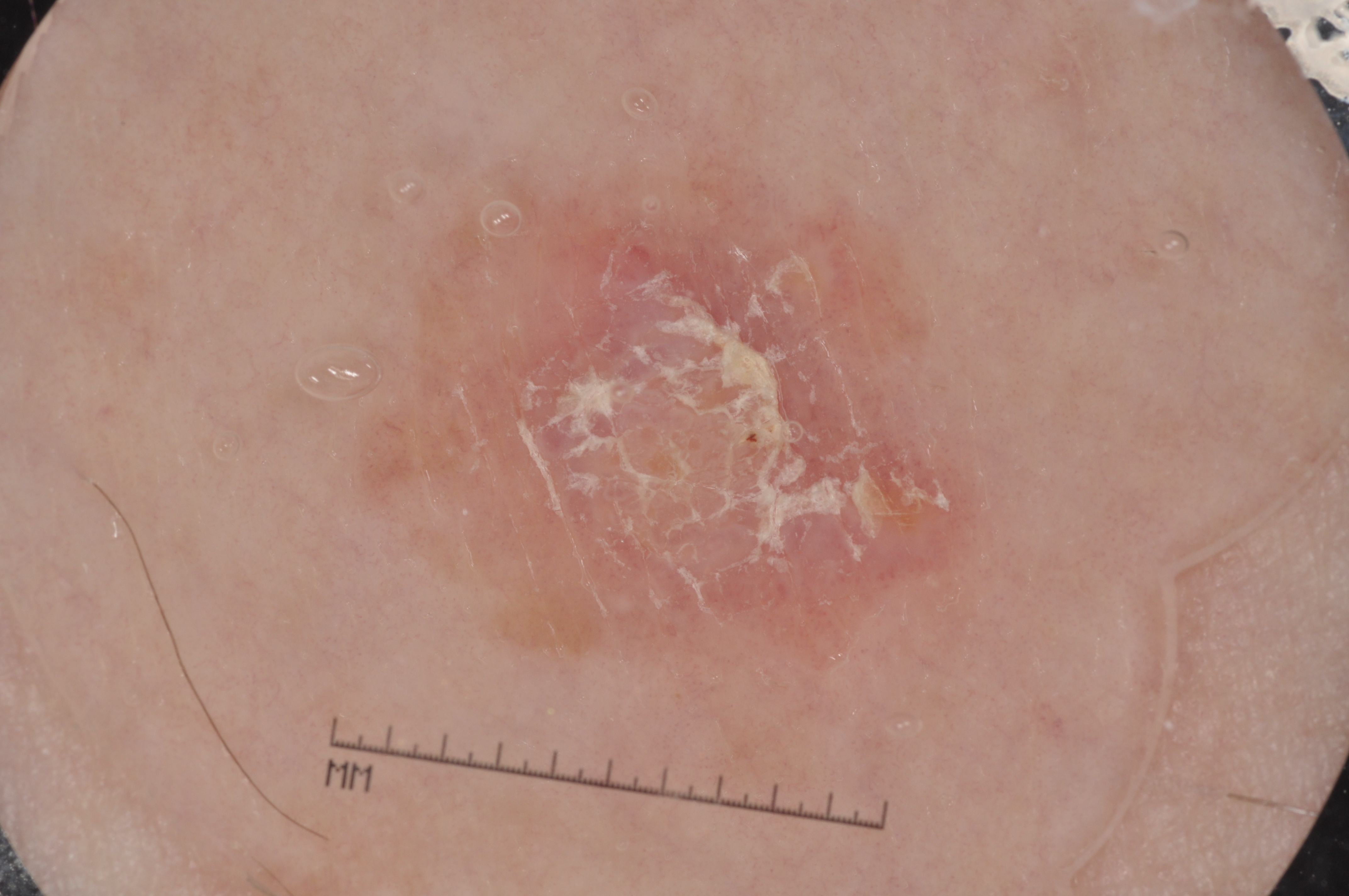Summary: A dermoscopic image of a skin lesion. In (x1, y1, x2, y2) order, the lesion is bounded by bbox(348, 147, 1001, 679). Conclusion: Clinically diagnosed as a seborrheic keratosis, a benign skin lesion.